By self-report, no sunbed use and no personal history of cancer; a male patient 15 years old; the referring clinician suspected melanocytic nevus; the patient says their skin tans without first burning:
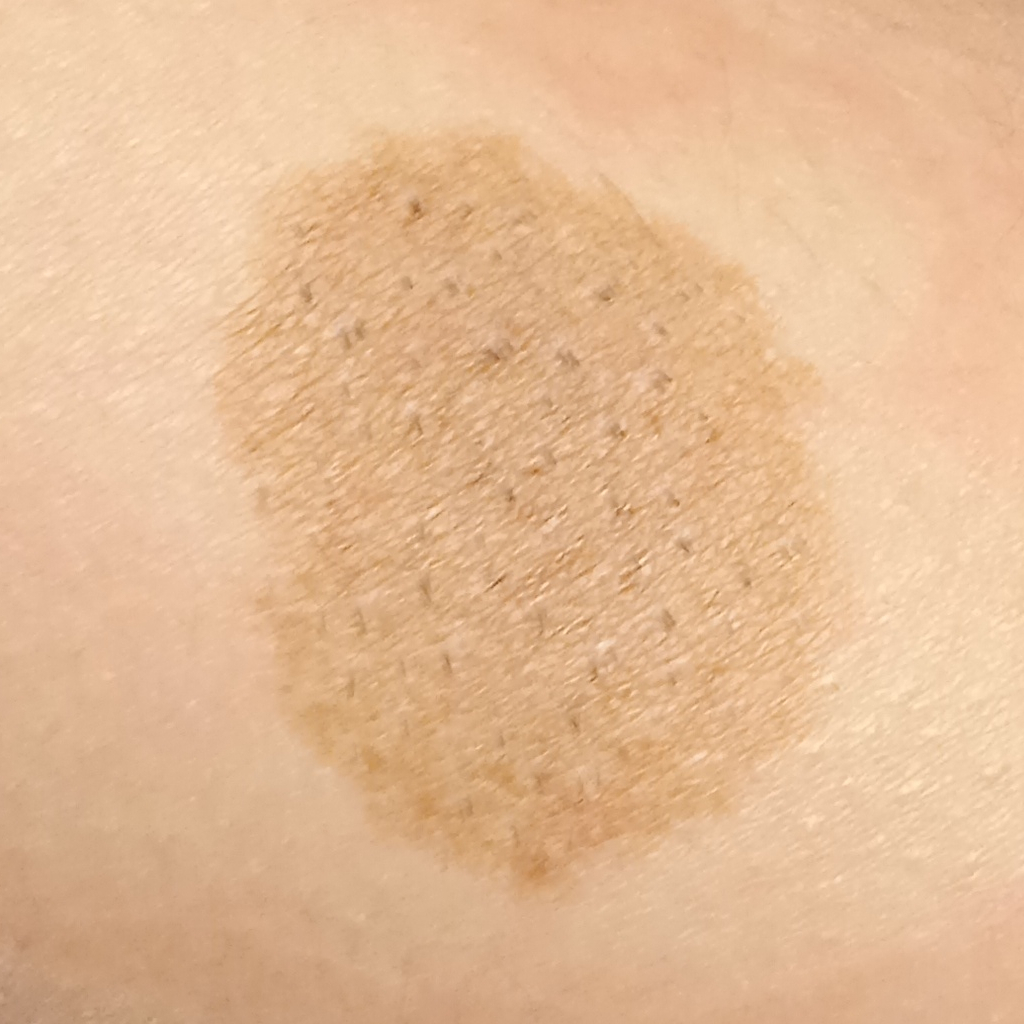* location: an arm
* diagnostic label: melanocytic nevus (biopsy-proven)